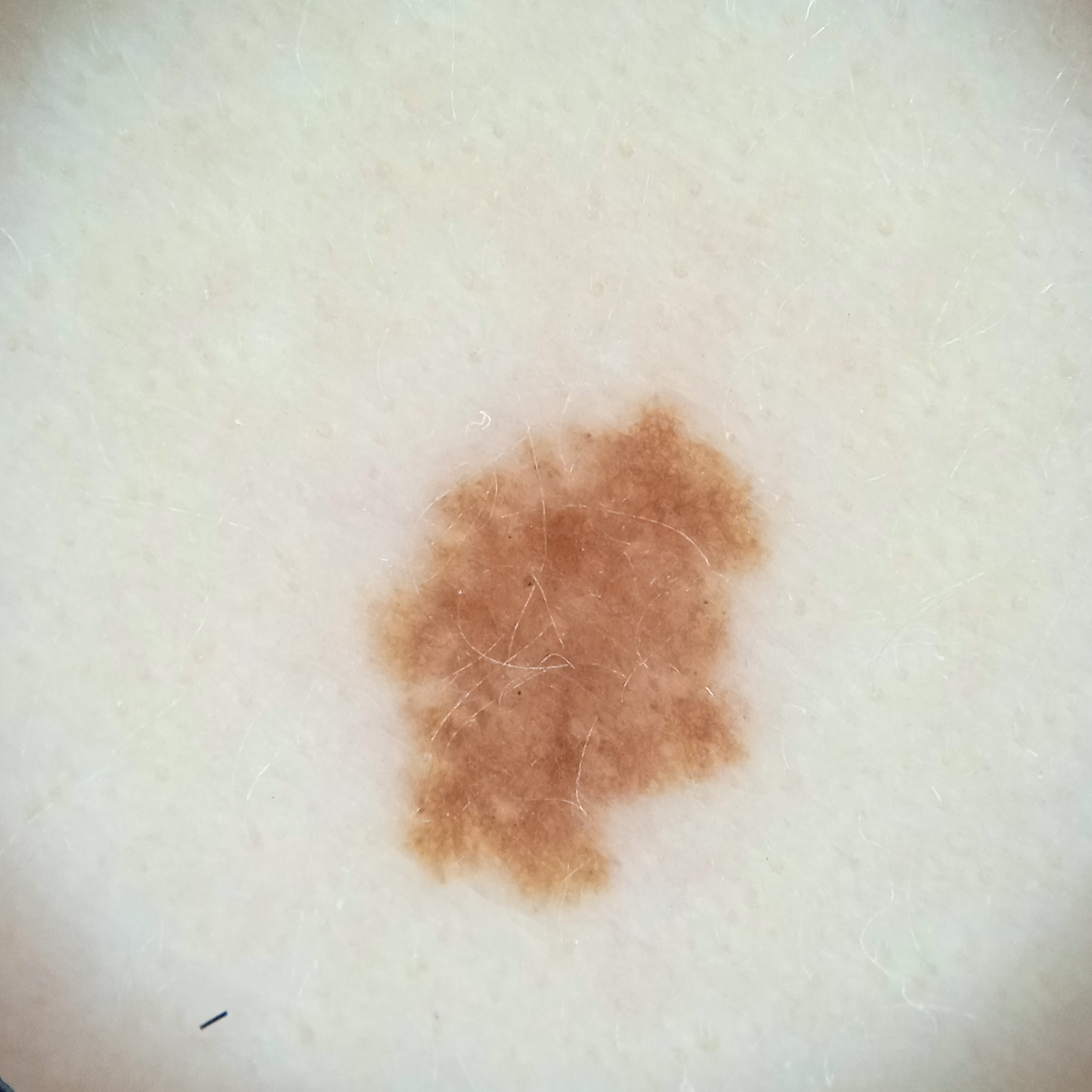A female subject 27 years of age.
Imaged for a research study, with no referral diagnosis recorded.
The patient describes having a moderate number of moles.
The patient says their skin reddens with sun exposure.
A dermatoscopic image of a skin lesion.
The lesion involves an arm.
The lesion measures approximately 6.4 mm.
The consensus diagnosis for this lesion was an atypical (dysplastic) nevus.